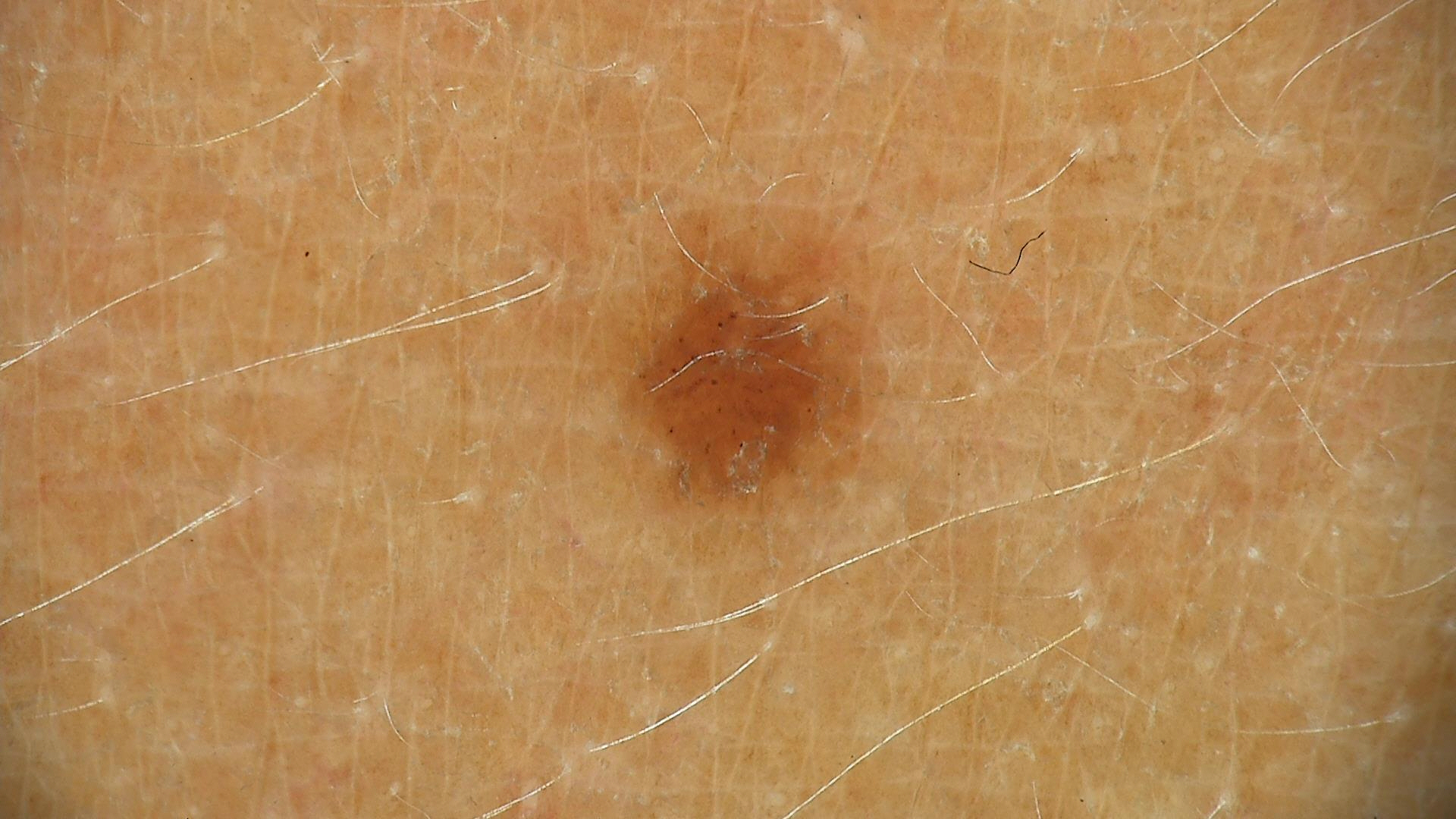Consistent with a seborrheic keratosis.